A dermoscopic view of a skin lesion · the patient is a female aged approximately 30:
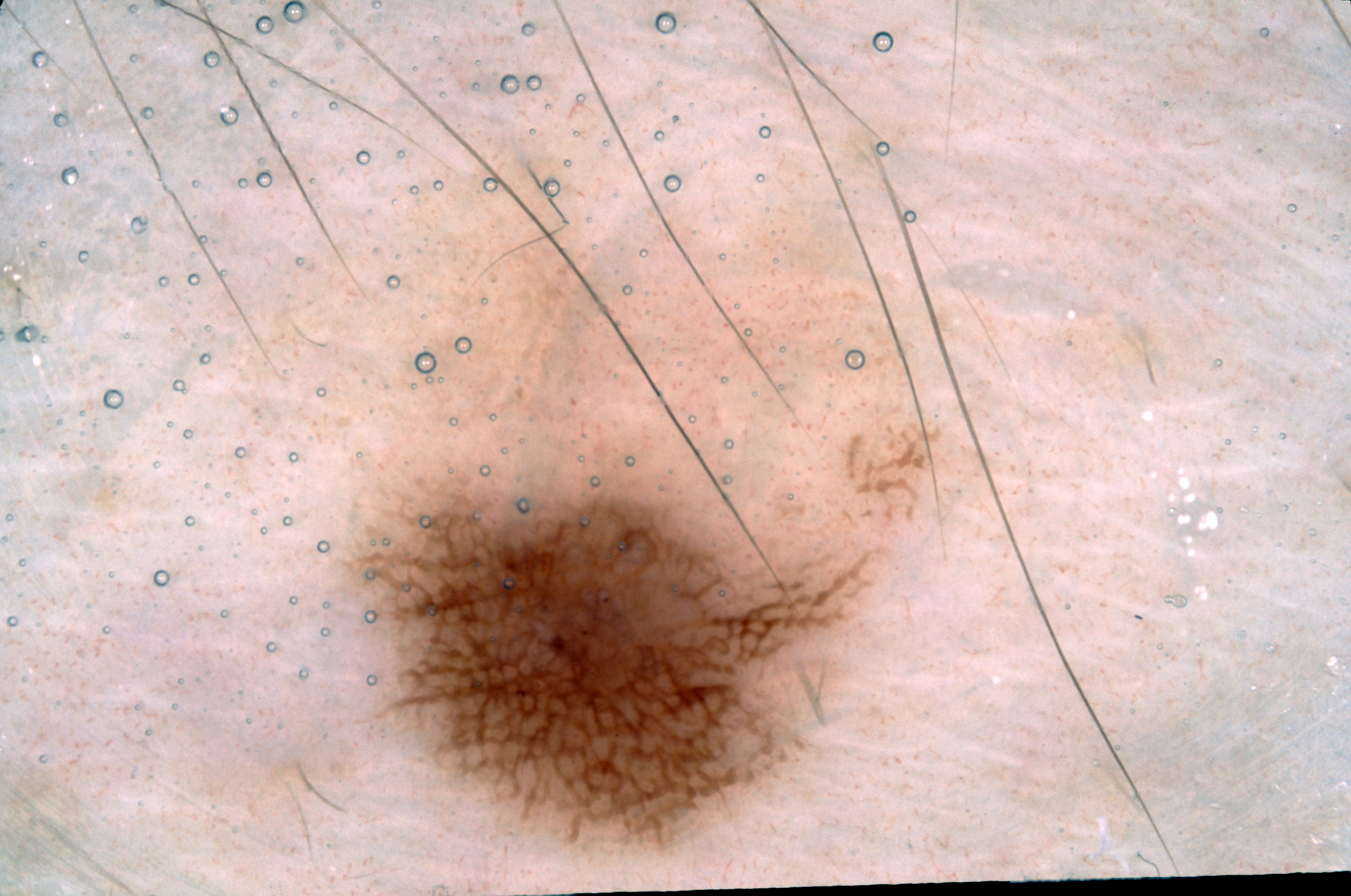As (left, top, right, bottom), the lesion spans 280/122/954/867. Dermoscopically, the lesion shows pigment network. The lesion covers approximately 32% of the dermoscopic field. The diagnostic assessment was a melanocytic nevus.